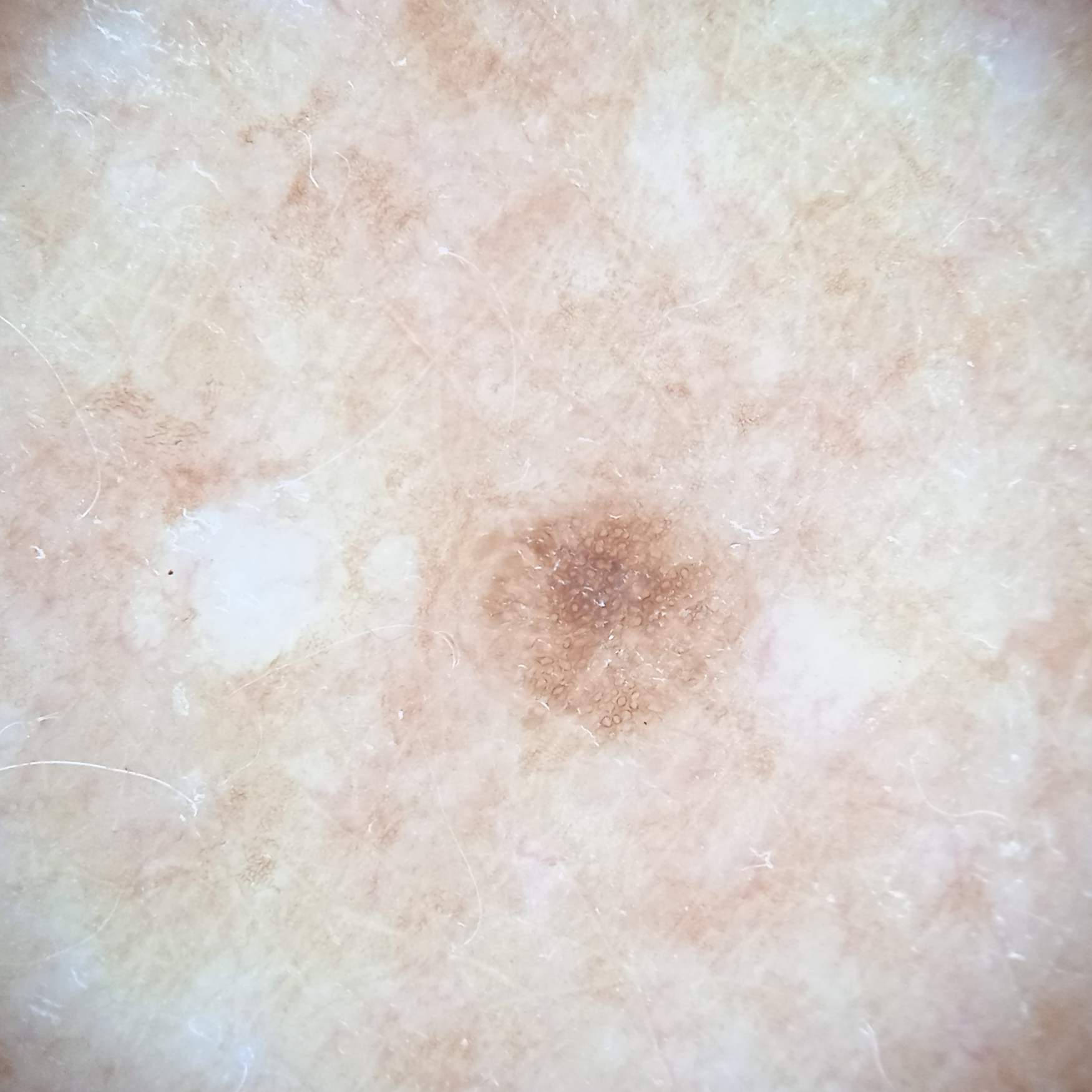Q: Patient demographics?
A: female, age 75
Q: What is the patient's nevus burden?
A: a moderate number of melanocytic nevi
Q: What are the relevant risk factors?
A: a personal history of skin cancer, a personal history of cancer
Q: Why was this imaged?
A: research study (no referral diagnosis)
Q: How large is the lesion?
A: 2.7 mm
Q: What was the diagnosis?
A: melanocytic nevus (dermatologist consensus)